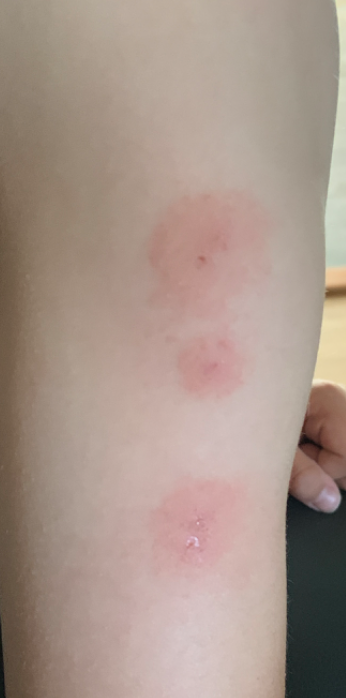Findings:
Eczema (most likely).